The lesion involves the leg. The photo was captured at a distance. The contributor is 30–39, male — 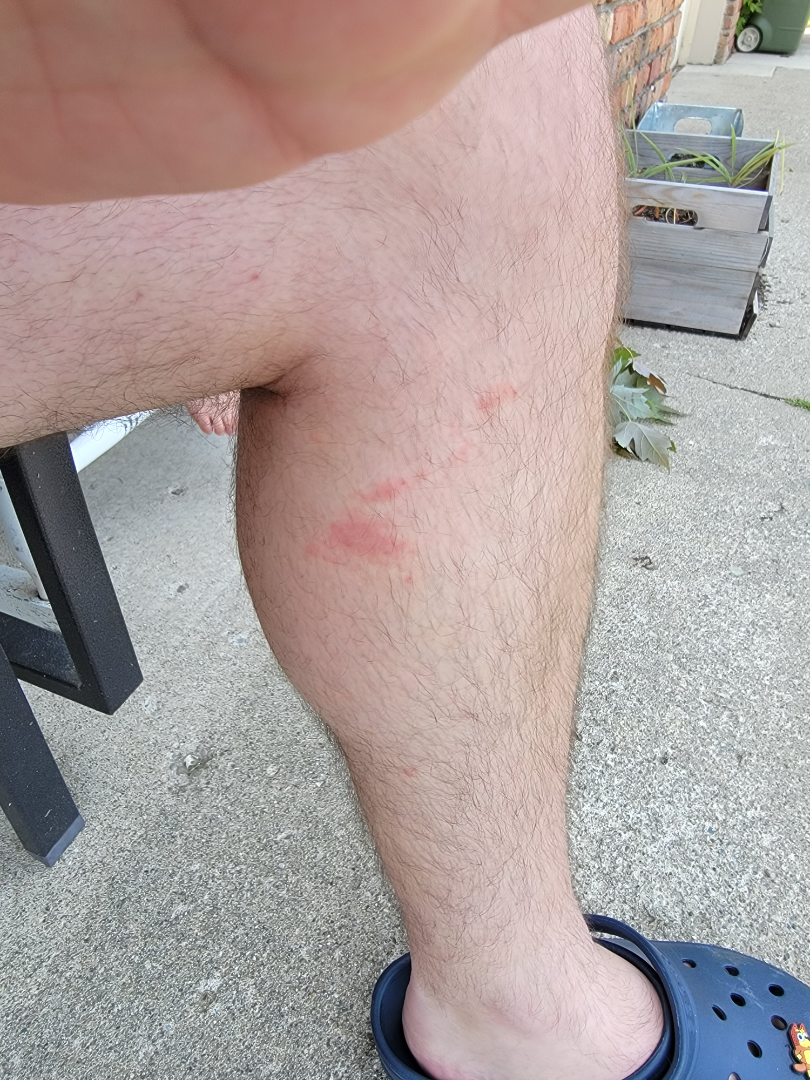Notes:
* assessment · indeterminate
* duration · less than one week
* patient describes the issue as · a rash
* skin tone · Fitzpatrick phototype II; human graders estimated Monk skin tone scale 1–2
* texture · raised or bumpy
* symptoms · enlargement and itching